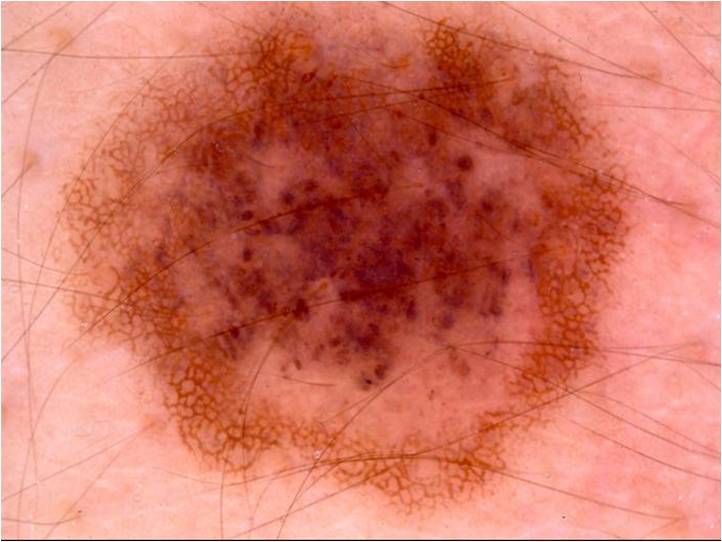patient = female, aged 73 to 77 | imaging = dermoscopic image | dermoscopic findings = pigment network and globules | lesion bbox = 51 3 640 526 | diagnostic label = a melanocytic nevus, a benign lesion.